An image taken at a distance. Lay reviewers estimated Monk Skin Tone 6 (US pool) or 5 (India pool):
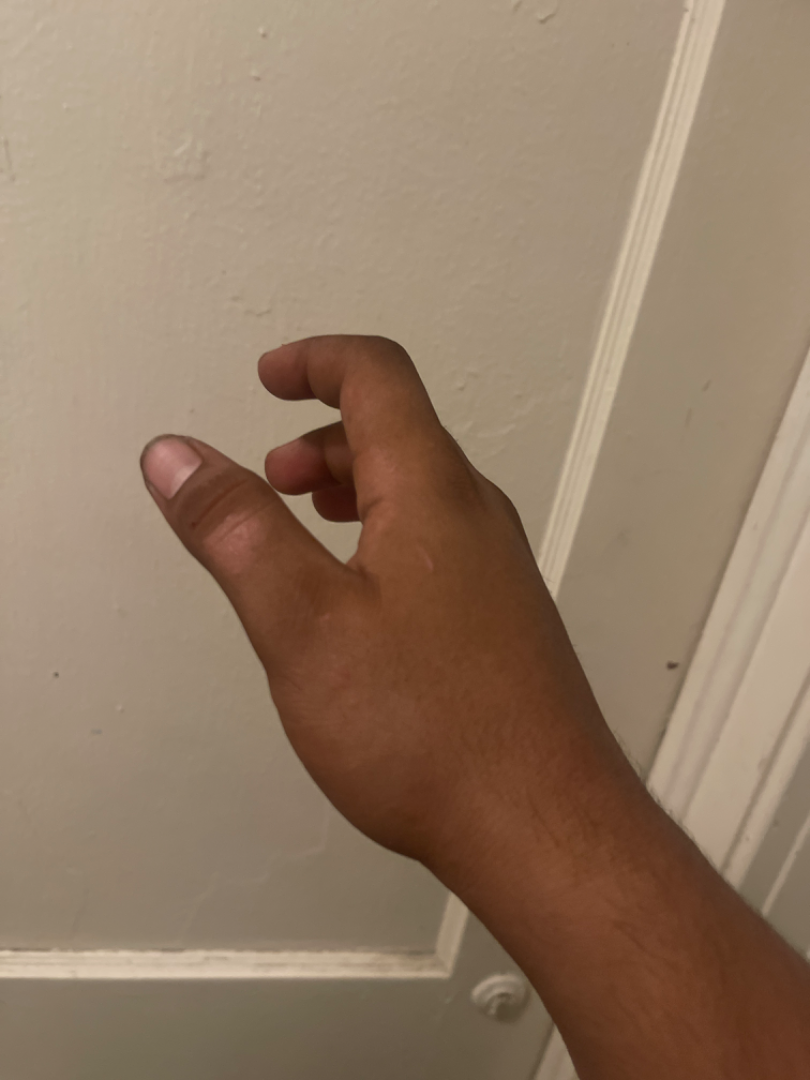assessment: unable to determine